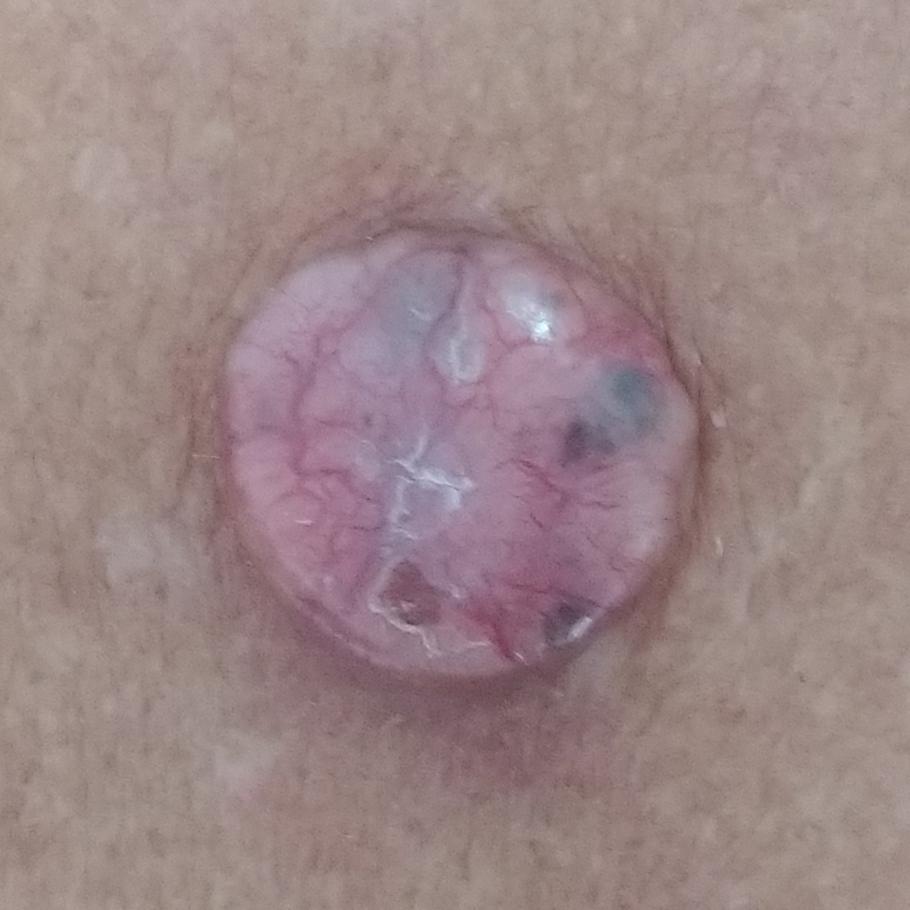A clinical photo of a skin lesion taken with a smartphone. A male subject 54 years old. The lesion involves the back. By the patient's account, the lesion is elevated and has grown. The biopsy diagnosis was a basal cell carcinoma.